This is a close-up image; the affected area is the arm and leg.
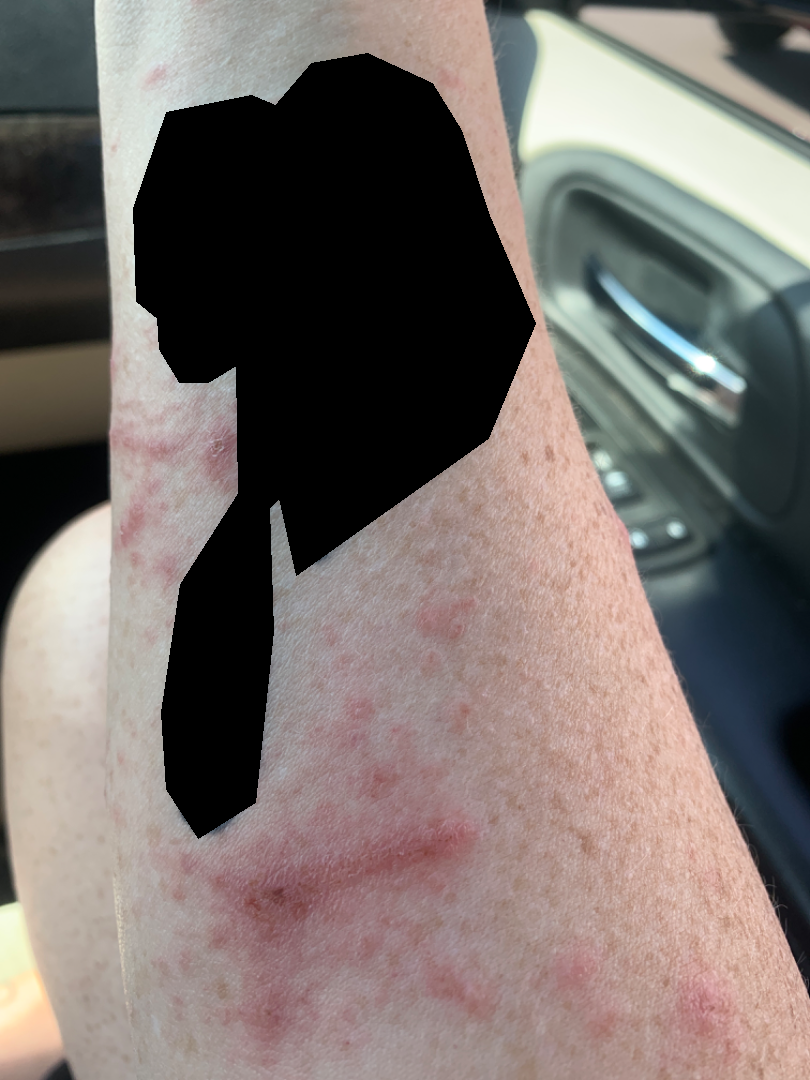Patient information: Reported lesion symptoms include burning and itching. Skin tone: Fitzpatrick skin type II; human graders estimated Monk skin tone scale 2. The contributor notes the condition has been present for one to four weeks. No associated systemic symptoms reported. The contributor notes the lesion is fluid-filled and raised or bumpy. The patient described the issue as a rash. Review: On photographic review: the impression on review was Allergic Contact Dermatitis.